The lesion involves the leg, an image taken at an angle — 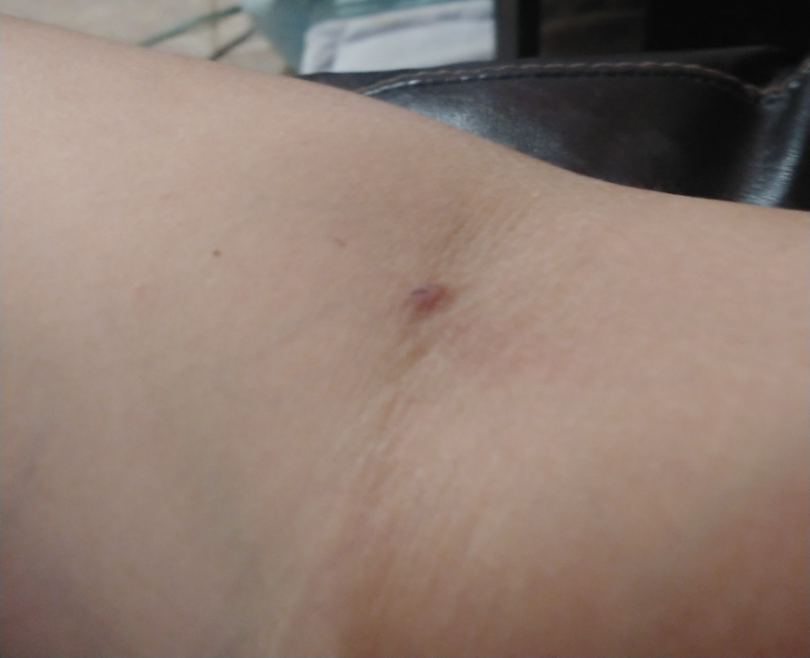<summary>
<assessment>not assessable</assessment>
<texture>fluid-filled, raised or bumpy</texture>
<duration>less than one week</duration>
<symptoms>pain, bothersome appearance, enlargement</symptoms>
<patient_category>acne</patient_category>
</summary>